The patient reports a personal history of cancer. A male patient 78 years of age. The patient says their skin reddens with sun exposure. Dermoscopy of a skin lesion. The patient describes having few moles overall. Imaged for a research study, with no referral diagnosis recorded: 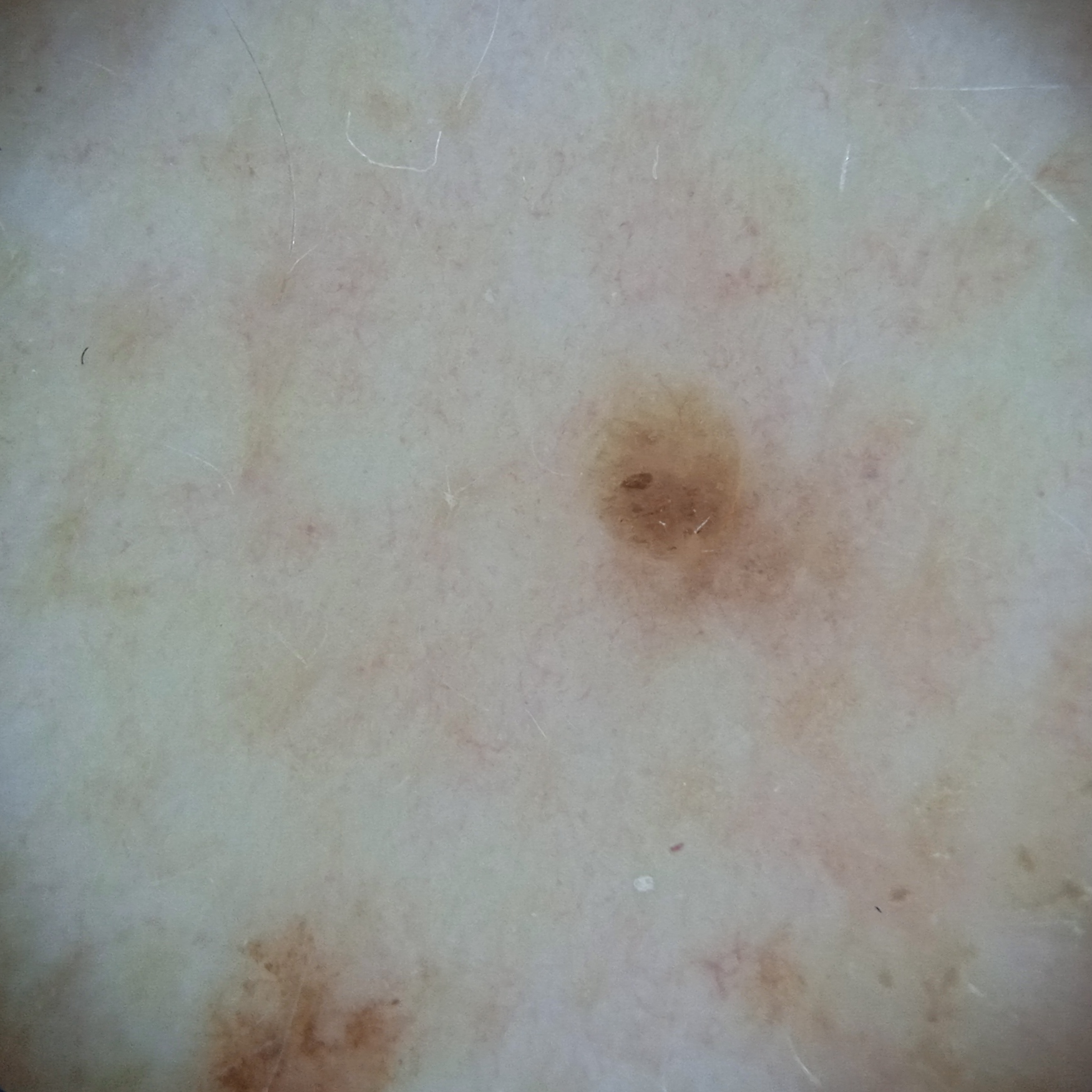Q: Where is the lesion?
A: the back
Q: How large is the lesion?
A: 3.1 mm
Q: What was the diagnosis?
A: seborrheic keratosis (dermatologist consensus)